A dermatoscopic image of a skin lesion:
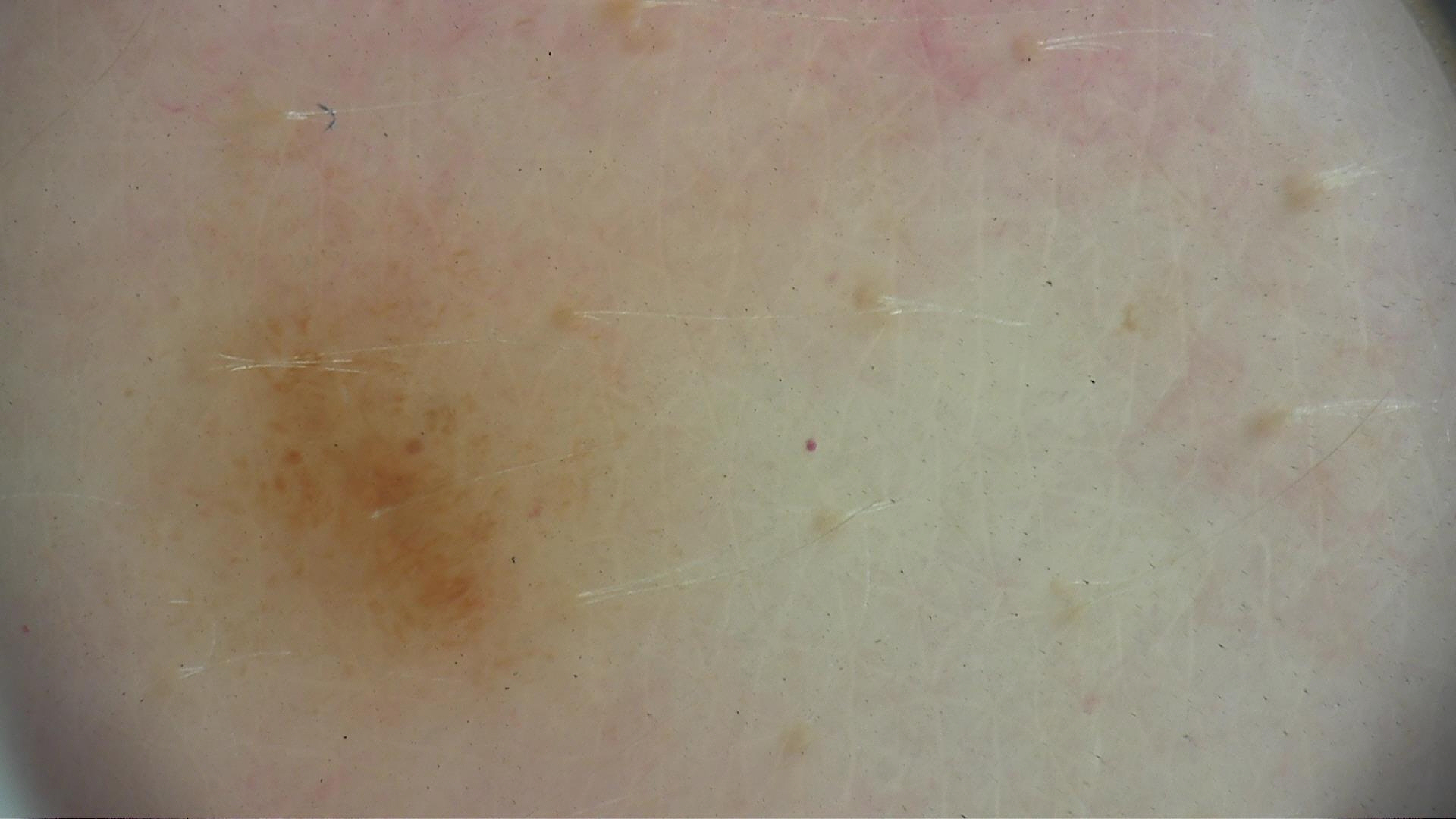Q: What is the diagnosis?
A: dysplastic junctional nevus (expert consensus)